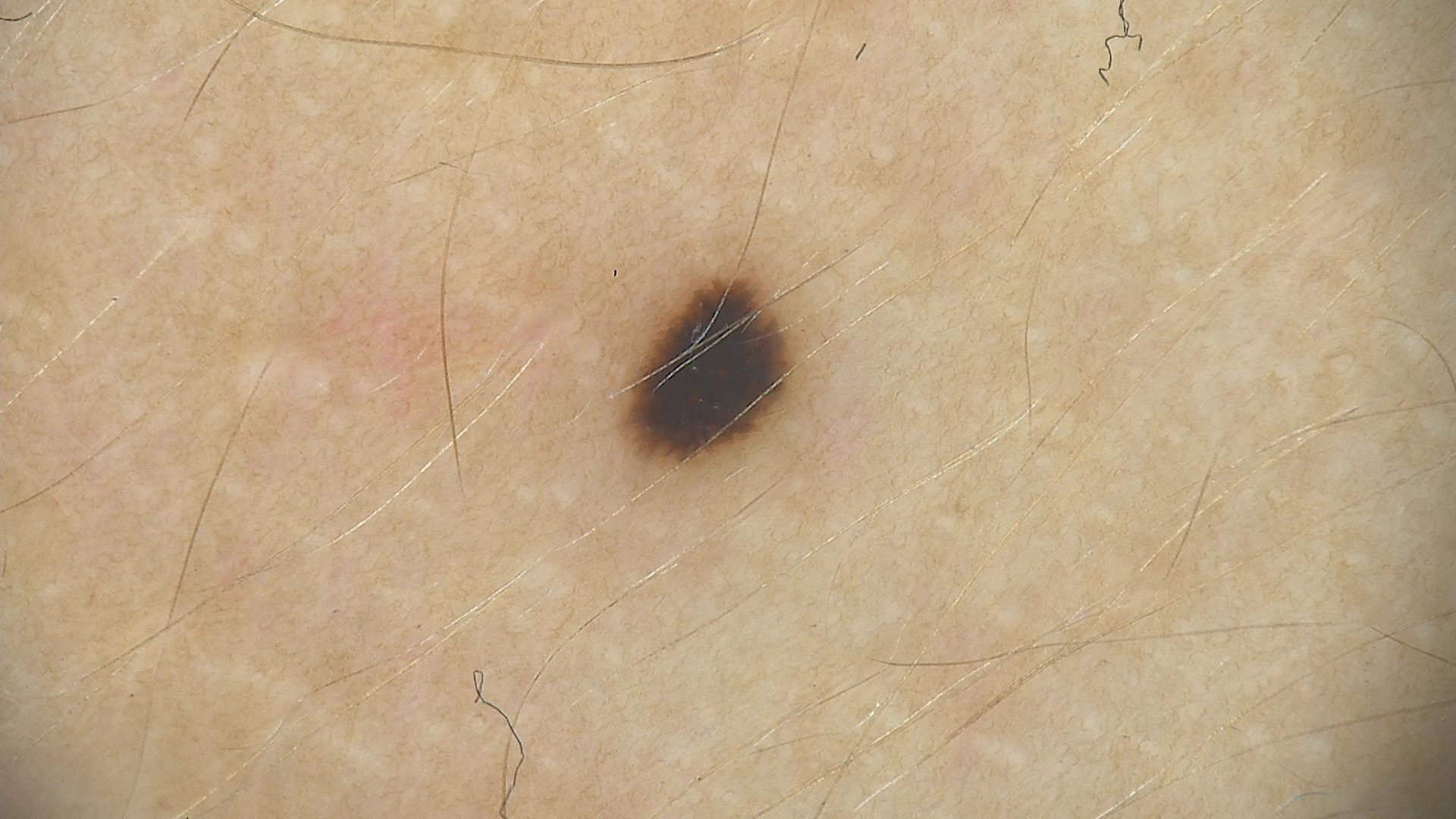Conclusion: Consistent with a Spitz/Reed nevus.